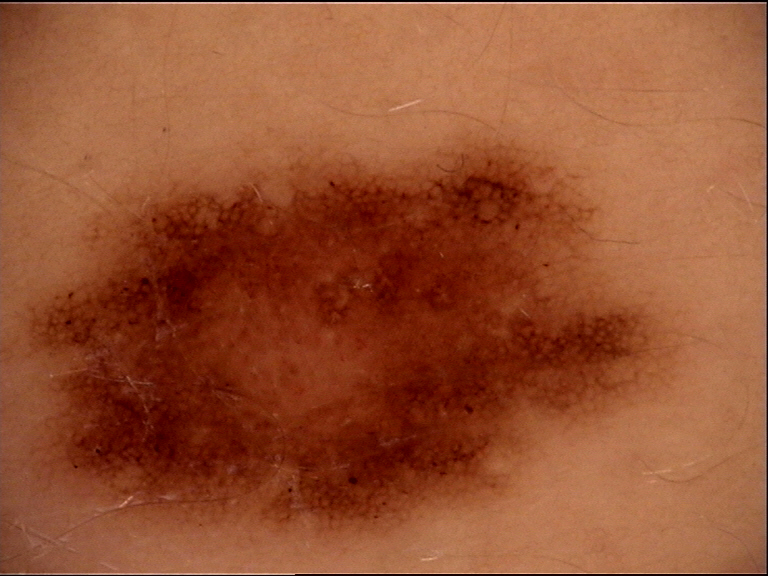A dermoscopy image of a single skin lesion. The diagnostic label was a dysplastic compound nevus.